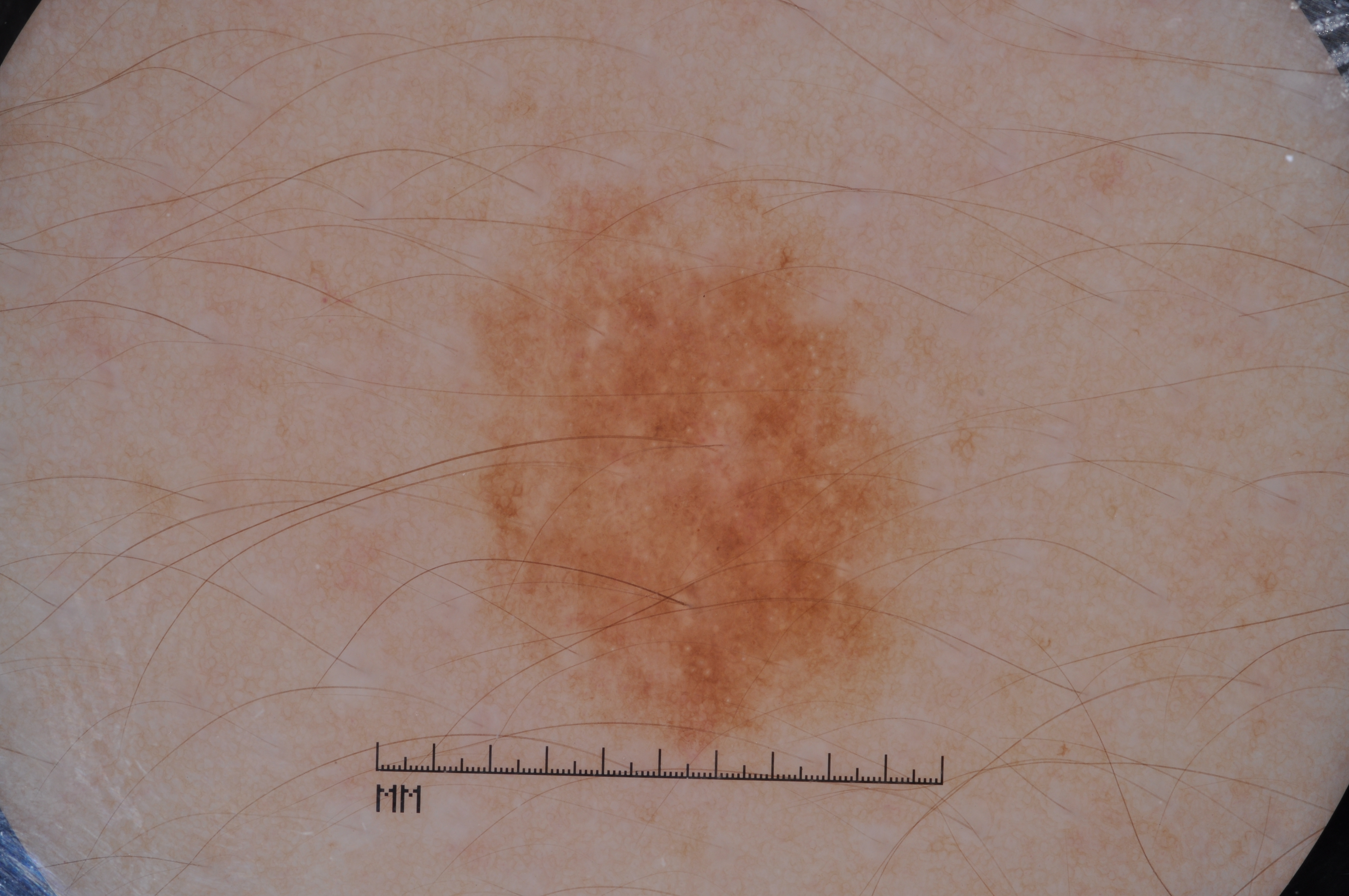A dermoscopy image of a single skin lesion. Dermoscopically, the lesion shows milia-like cysts. The lesion occupies roughly 15% of the field. With coordinates (x1, y1, x2, y2), the lesion's extent is box(464, 196, 916, 749). The lesion was assessed as a melanocytic nevus, a benign skin lesion.